A dermoscopic image of a skin lesion.
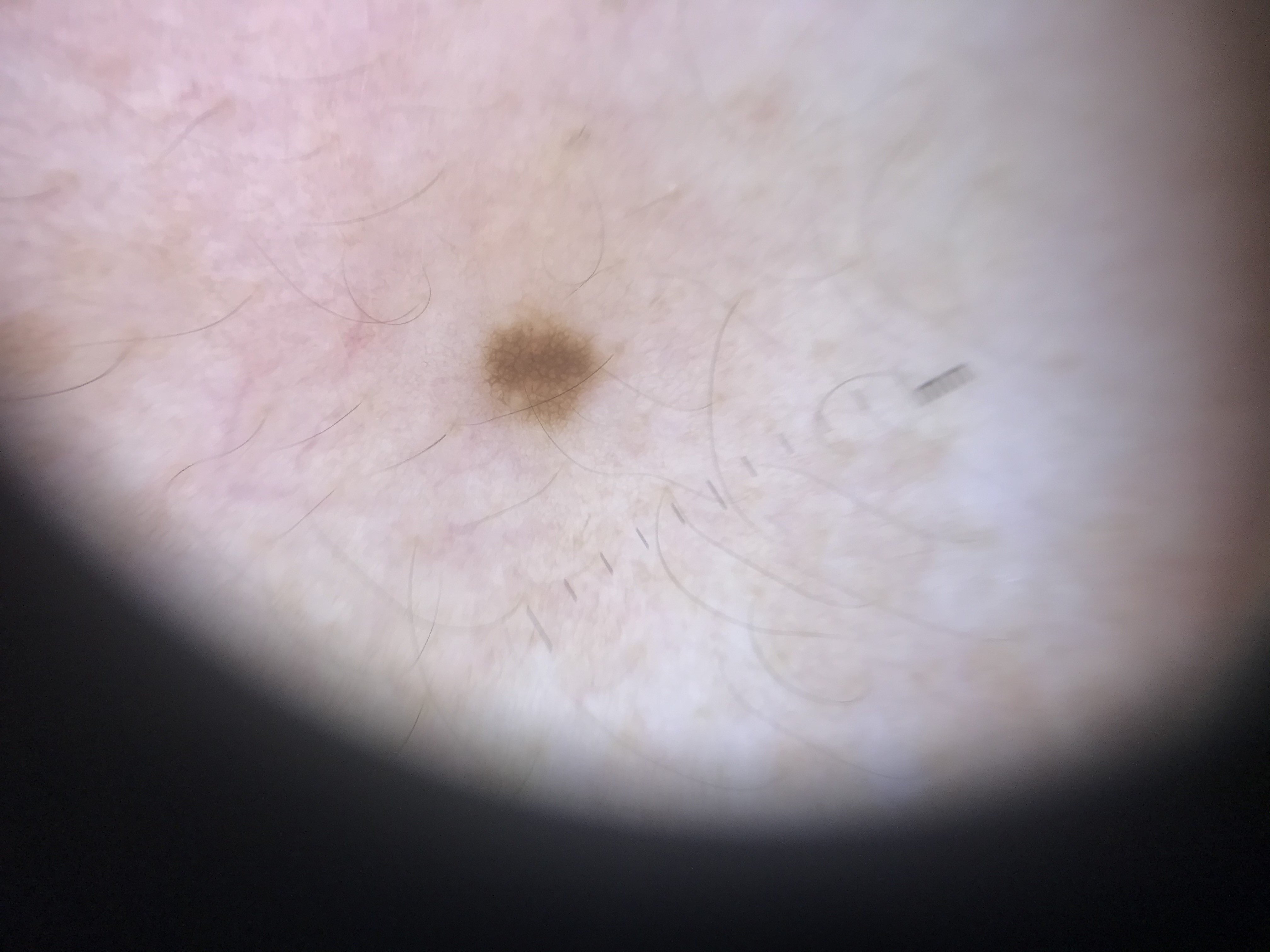Impression: Diagnosed as a banal lesion — a junctional nevus.